This image was taken at an angle · the head or neck is involved.
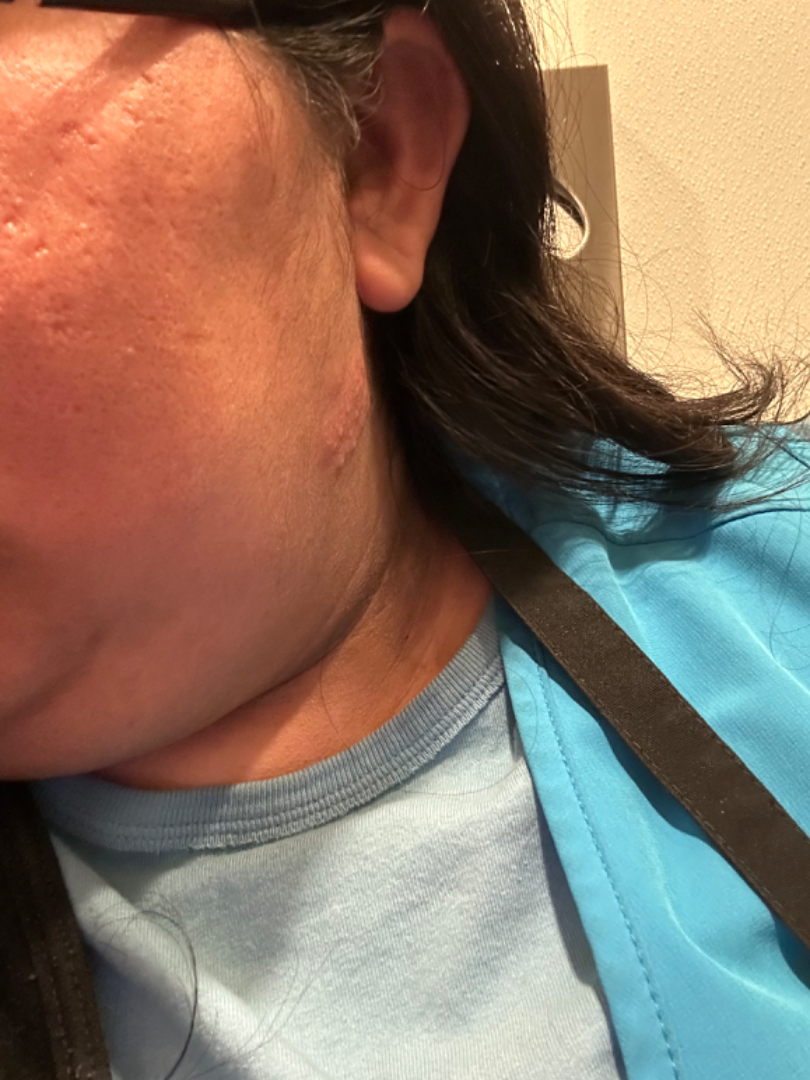impression: in keeping with Herpes Simplex.